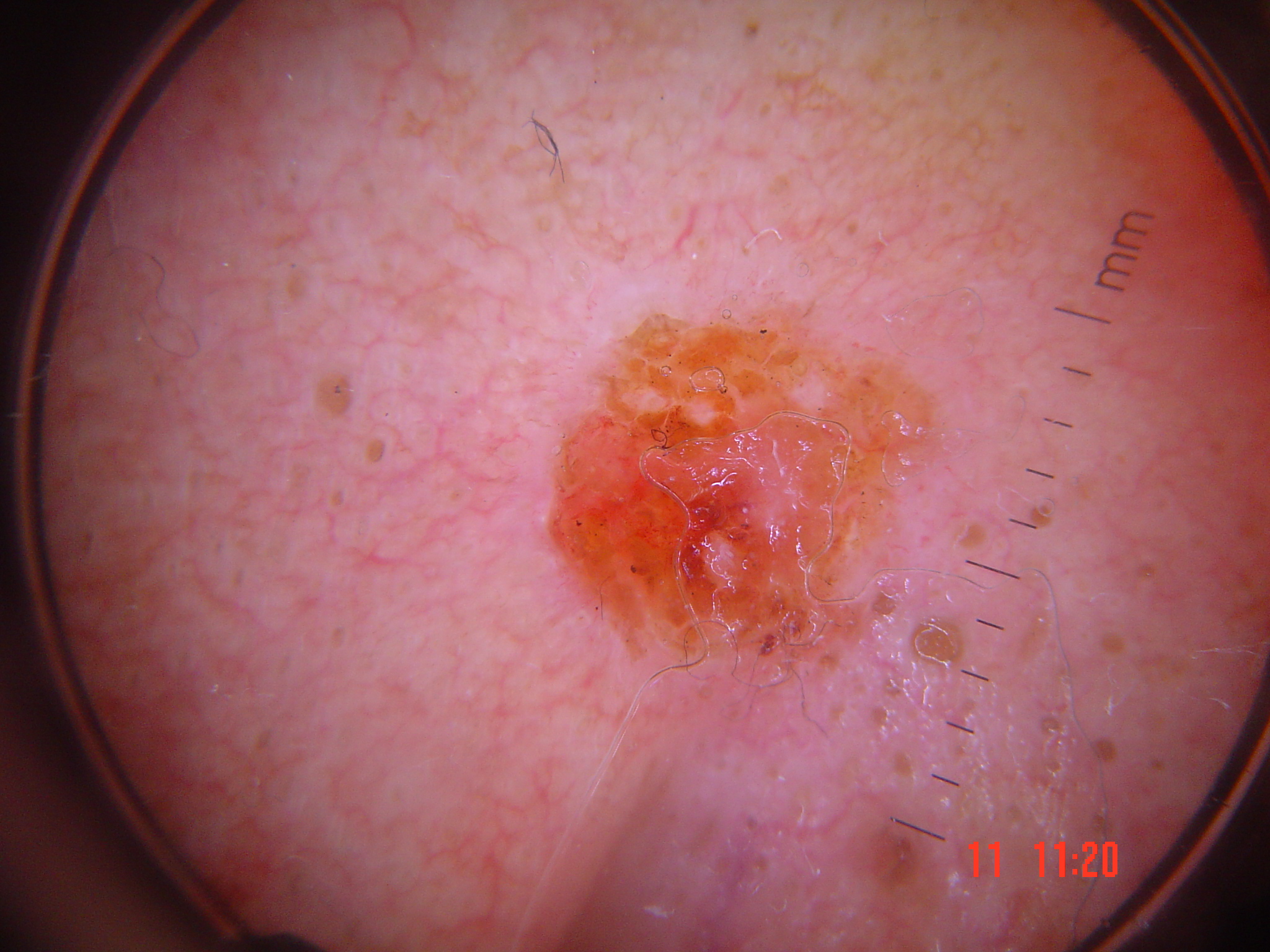image type — dermoscopy
label — squamous cell carcinoma (biopsy-proven)